The photograph was taken at an angle · located on the arm · the patient reported no systemic symptoms · the lesion is described as raised or bumpy · reported duration is one to three months · the subject is 50–59, female: 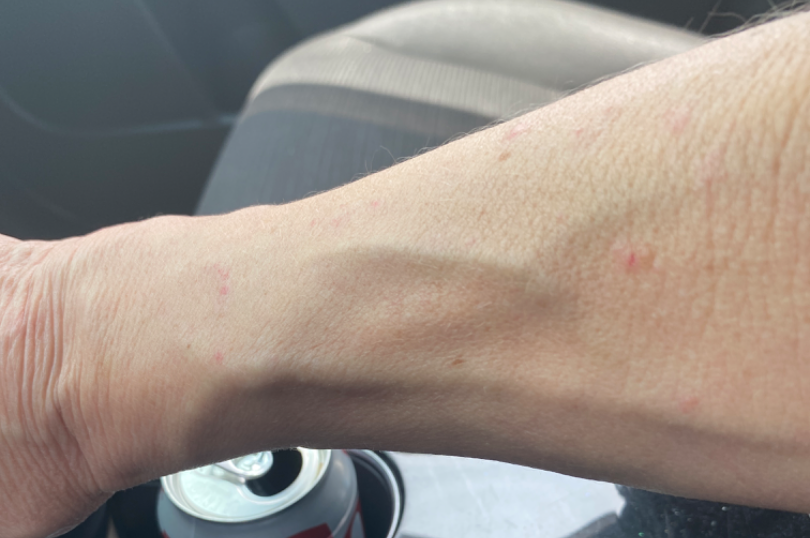Findings:
- assessment — ungradable on photographic review